A close-up photograph; the affected area is the leg; the patient is female — 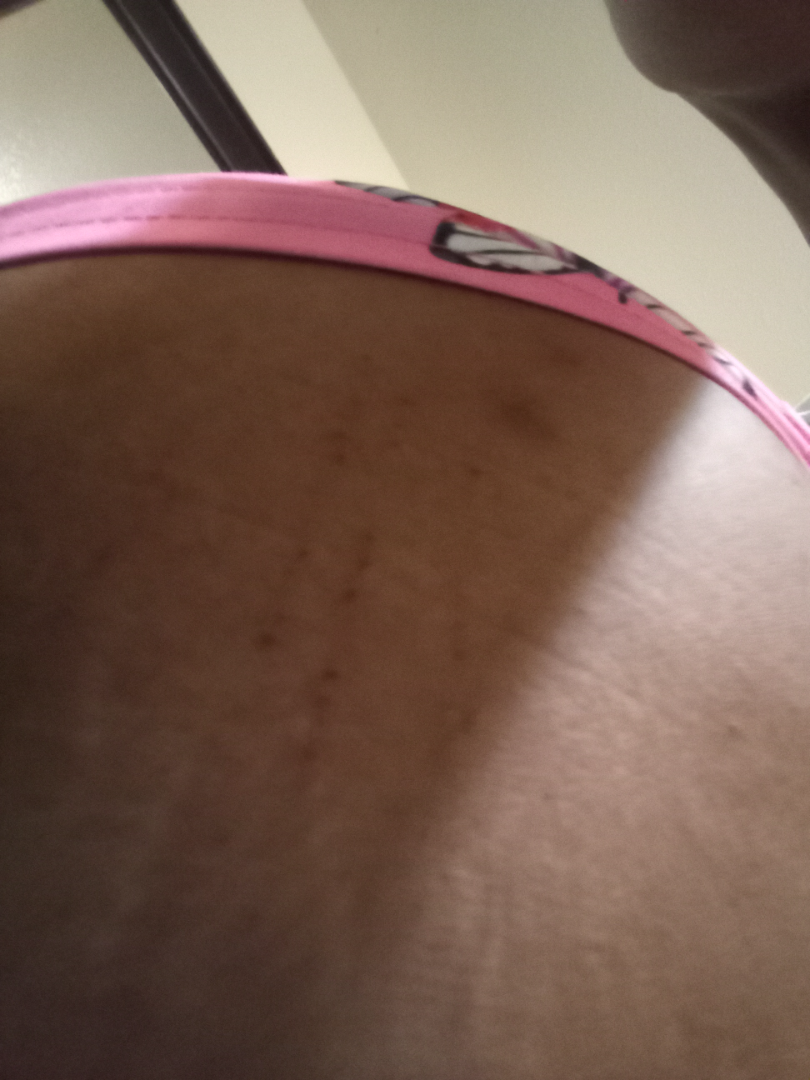The case was indeterminate on photographic review. Symptoms reported: darkening, itching and pain. Self-categorized by the patient as a rash. Self-reported FST IV; lay reviewers estimated MST 4 or 7 (two reviewer pools disagreed). The lesion is described as raised or bumpy, rough or flaky and flat.